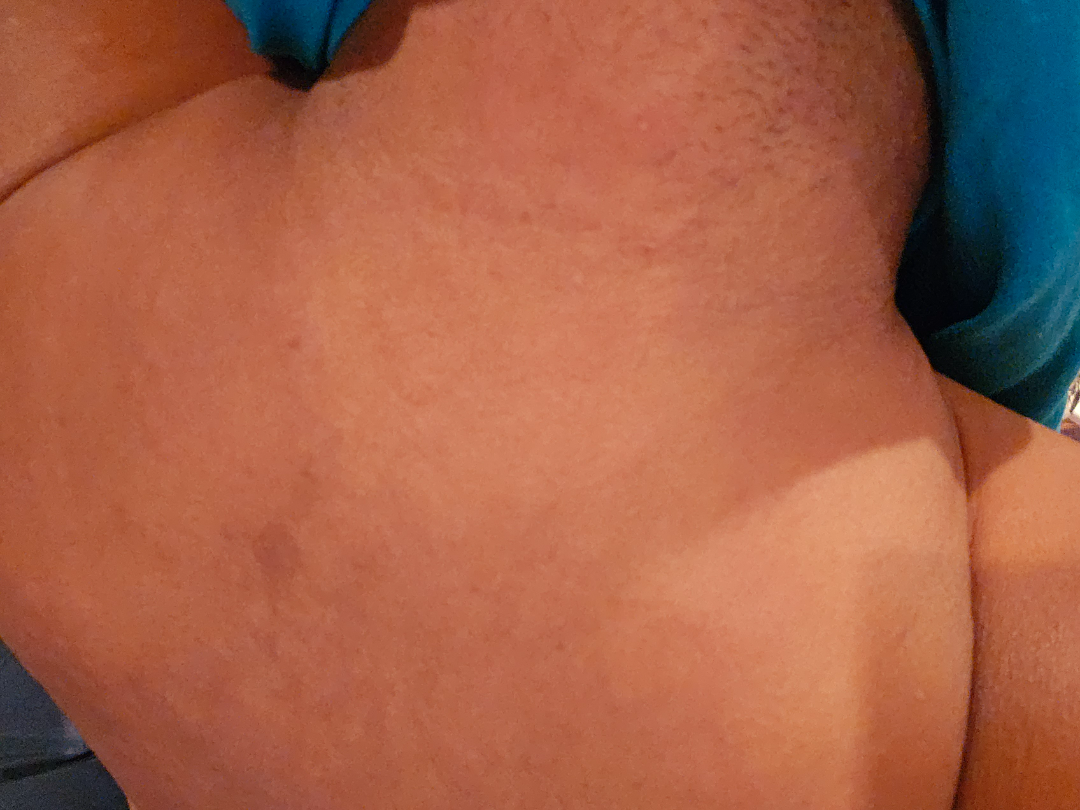Case summary:
• assessment: unable to determine
• skin tone: non-clinician graders estimated MST 4 or 6
• systemic symptoms: none reported
• patient describes the issue as: a rash
• texture: raised or bumpy
• body site: head or neck and arm
• shot type: at a distance